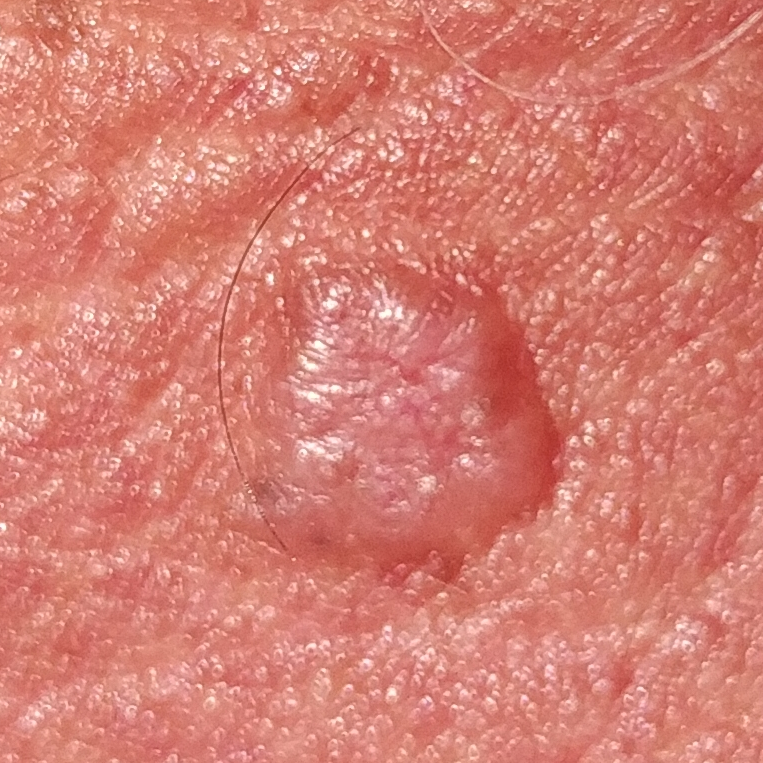image: clinical photo
patient:
  age: 58
  gender: male
risk_factors:
  positive:
    - smoking
    - prior cancer (patient or family)
    - alcohol use
    - pesticide exposure
skin_type: II
lesion_location: the nose
symptoms:
  present:
    - elevation
    - growth
diagnosis:
  name: basal cell carcinoma
  code: BCC
  malignancy: malignant
  confirmation: histopathology